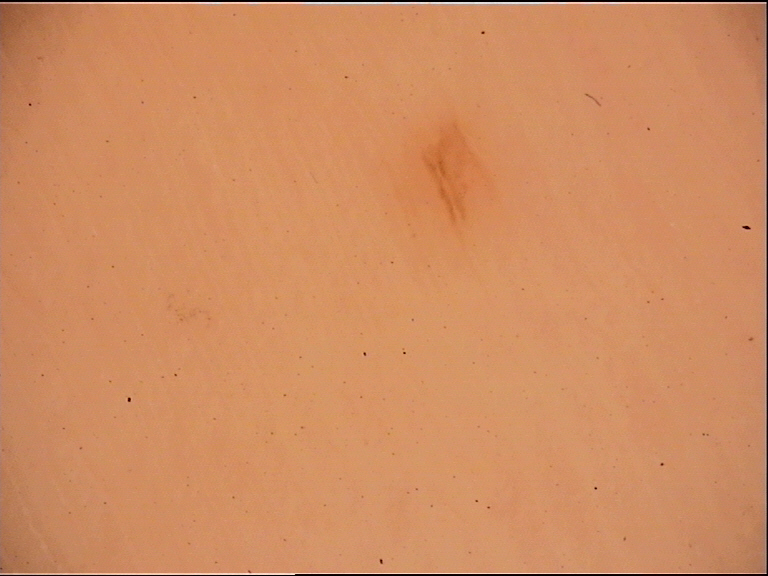{
  "image": "dermoscopy",
  "lesion_type": {
    "main_class": "banal",
    "pattern": "junctional"
  },
  "diagnosis": {
    "name": "acral junctional nevus",
    "code": "ajb",
    "malignancy": "benign",
    "super_class": "melanocytic",
    "confirmation": "expert consensus"
  }
}